Reported duration is one to four weeks; the patient notes associated joint pain, fever and fatigue; the affected area is the arm; this is a close-up image; symptoms reported: bleeding, enlargement, burning, bothersome appearance, darkening, pain and itching; the patient notes the lesion is fluid-filled; the subject is 50–59, female — 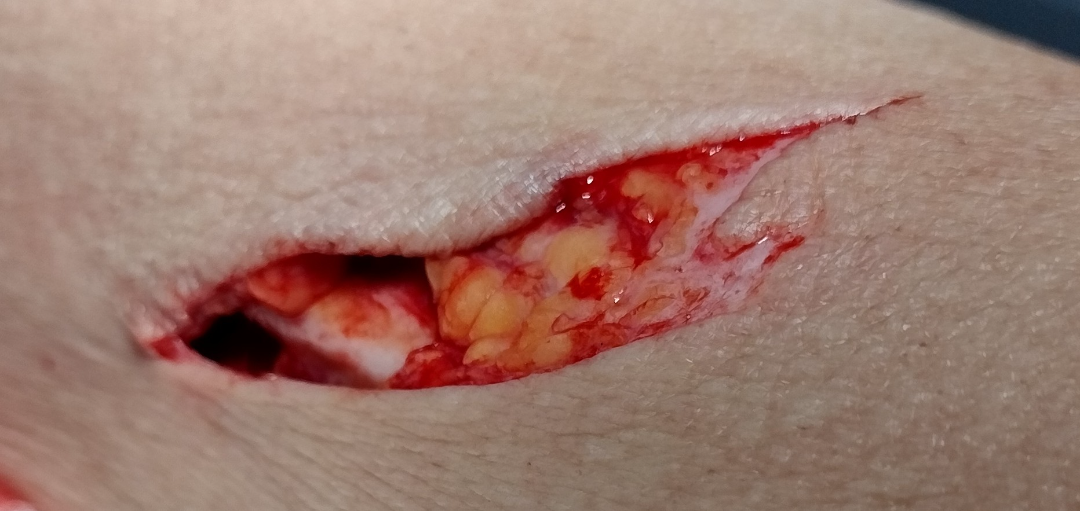Q: What is the differential diagnosis?
A: Inflicted skin lesions (most likely); Skin ulcer (considered); Dehiscence (considered)